The photograph is a close-up of the affected area:
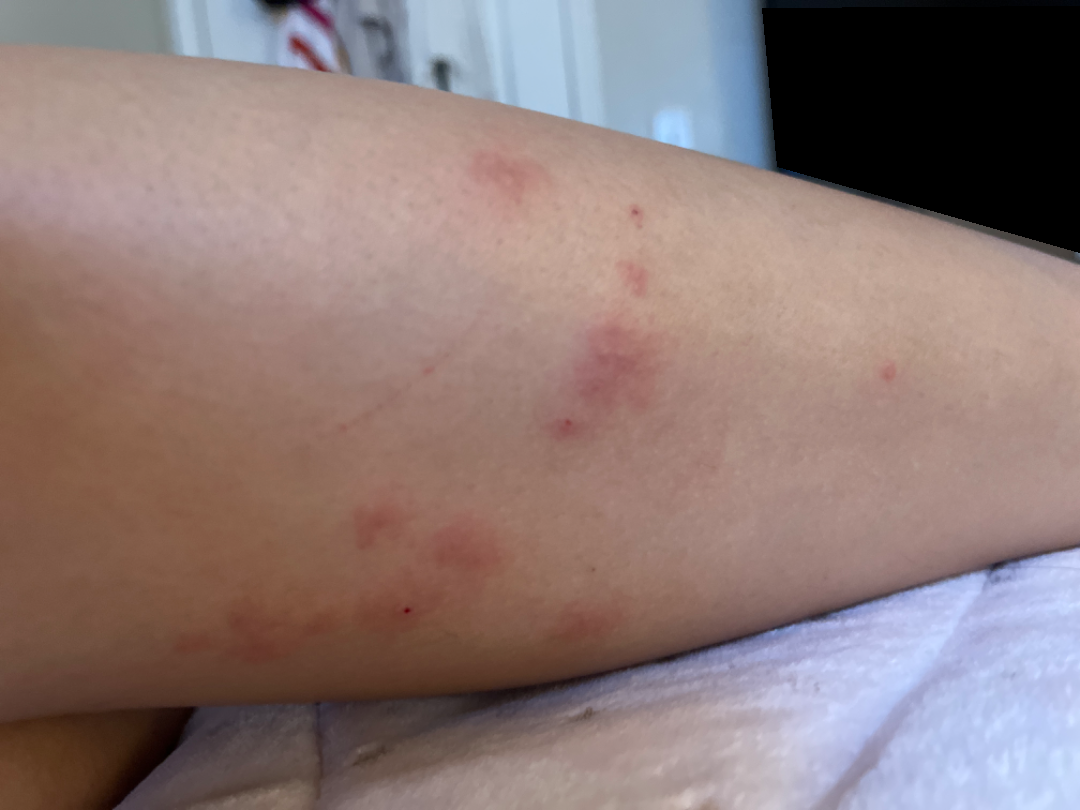{"assessment": "ungradable on photographic review"}